The contributor is 60–69, female; an image taken at a distance: 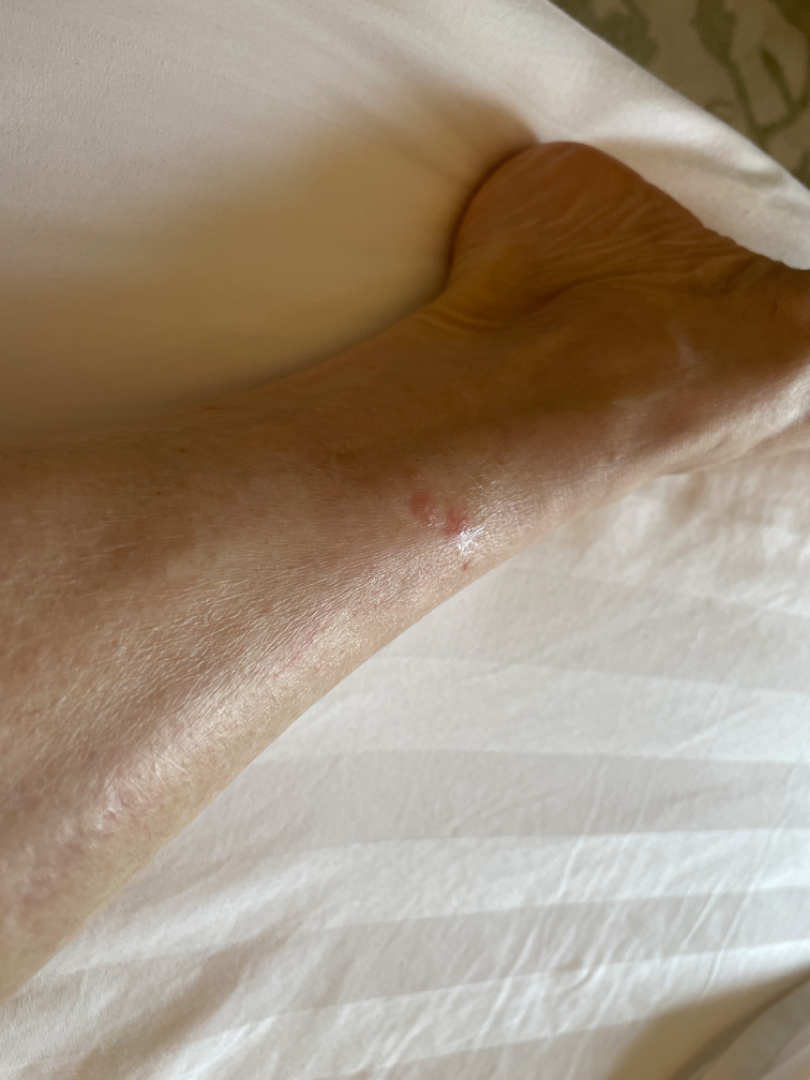Notes:
* assessment — could not be assessed